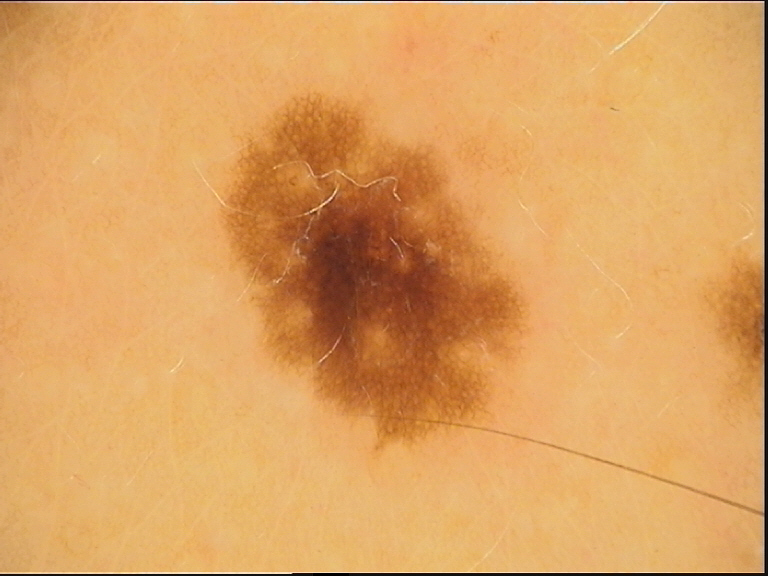A dermoscopic photograph of a skin lesion. Classified as a benign lesion — a dysplastic junctional nevus.